Close-up view; the lesion involves the leg and head or neck.
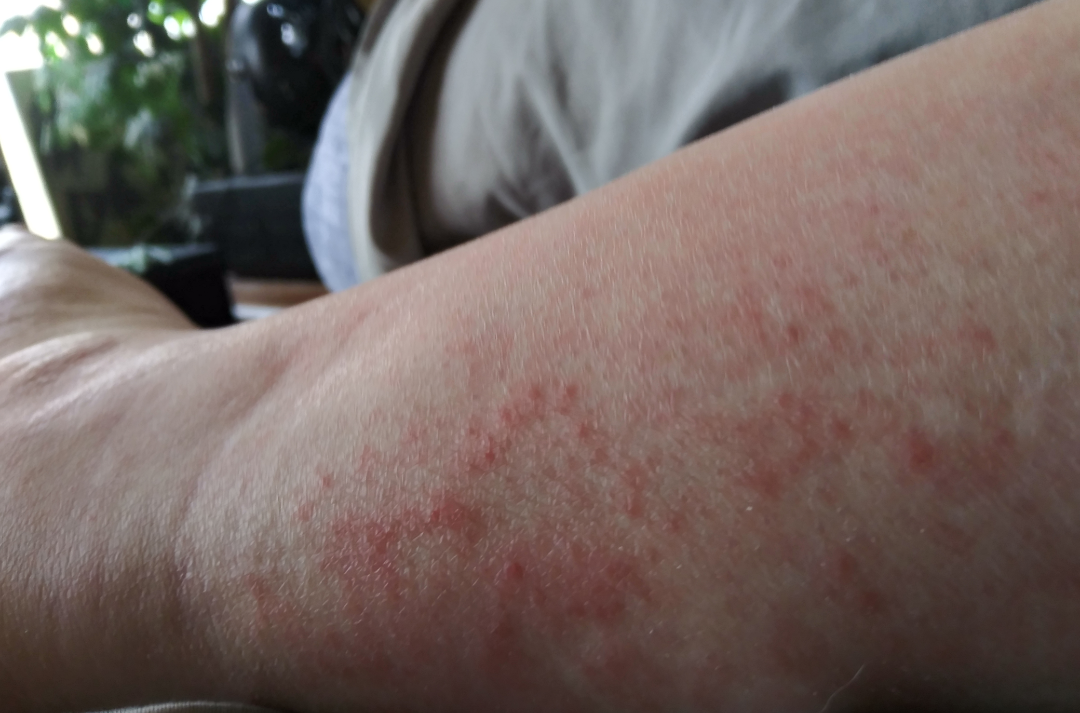assessment = indeterminate from the photograph | history = one to four weeks | lesion symptoms = bothersome appearance, enlargement, burning and itching | described texture = raised or bumpy | systemic symptoms = none reported.